Located on the back of the hand, back of the torso, arm and front of the torso; the subject is a female aged 50–59; the photograph is a close-up of the affected area:
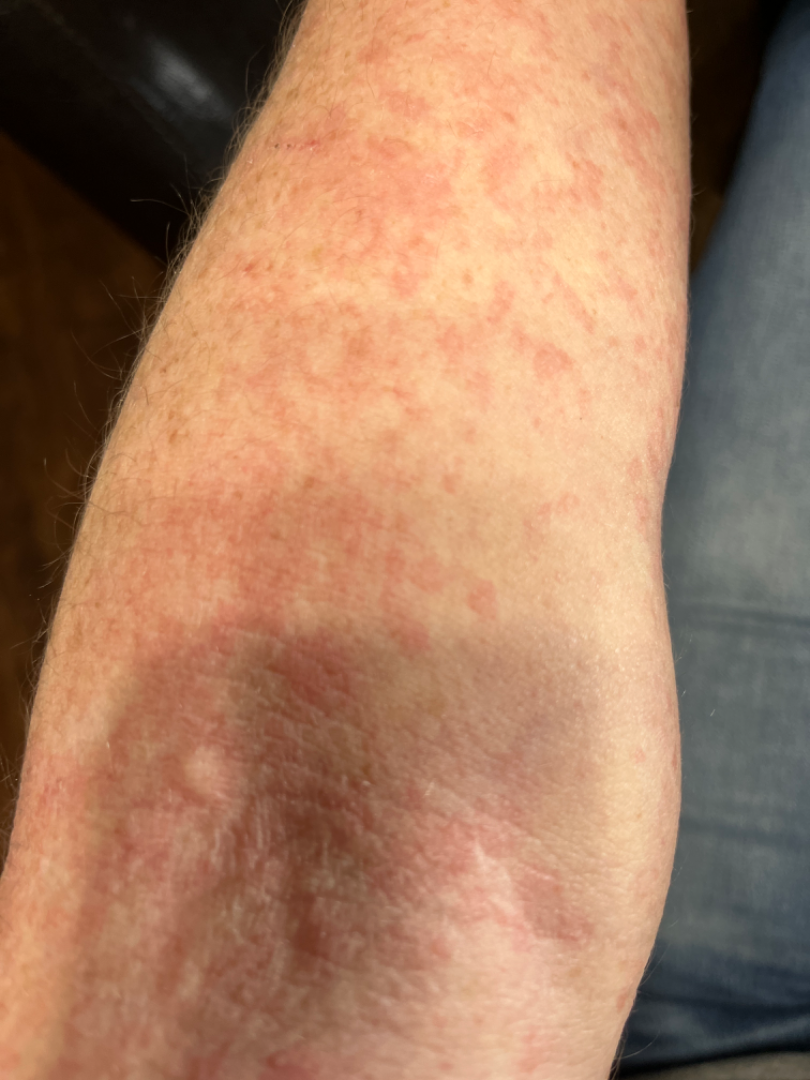| field | value |
|---|---|
| assessment | ungradable on photographic review |
| systemic symptoms | fatigue and joint pain |
| reported symptoms | bothersome appearance, itching and burning |
| skin tone | Fitzpatrick phototype III; human graders estimated 3 on the Monk Skin Tone |
| surface texture | raised or bumpy |
| onset | less than one week |